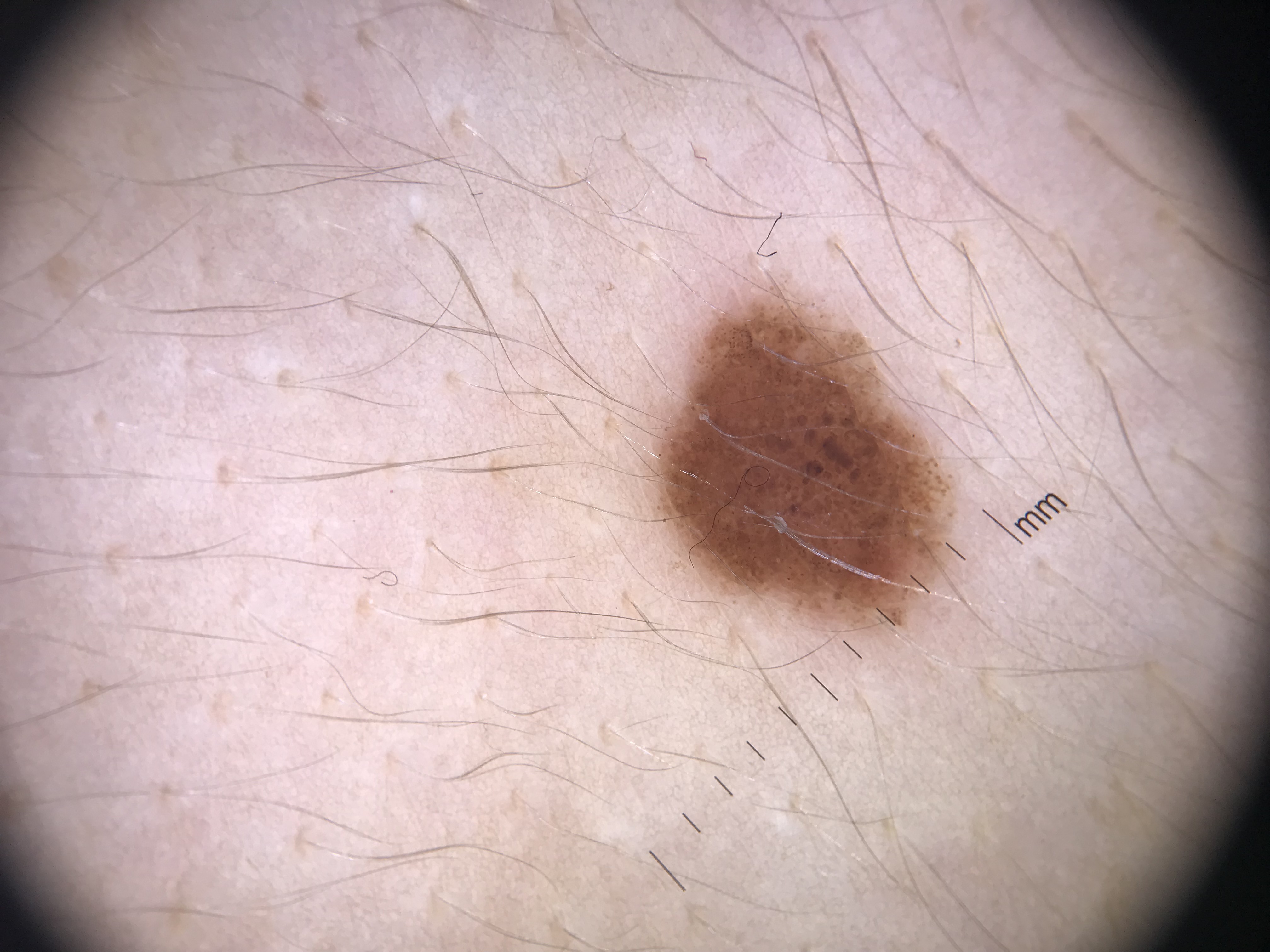image: dermoscopy
lesion type: banal
assessment: compound nevus (expert consensus)